The patient is a female aged 18–29, an image taken at a distance, the affected area is the arm and leg — 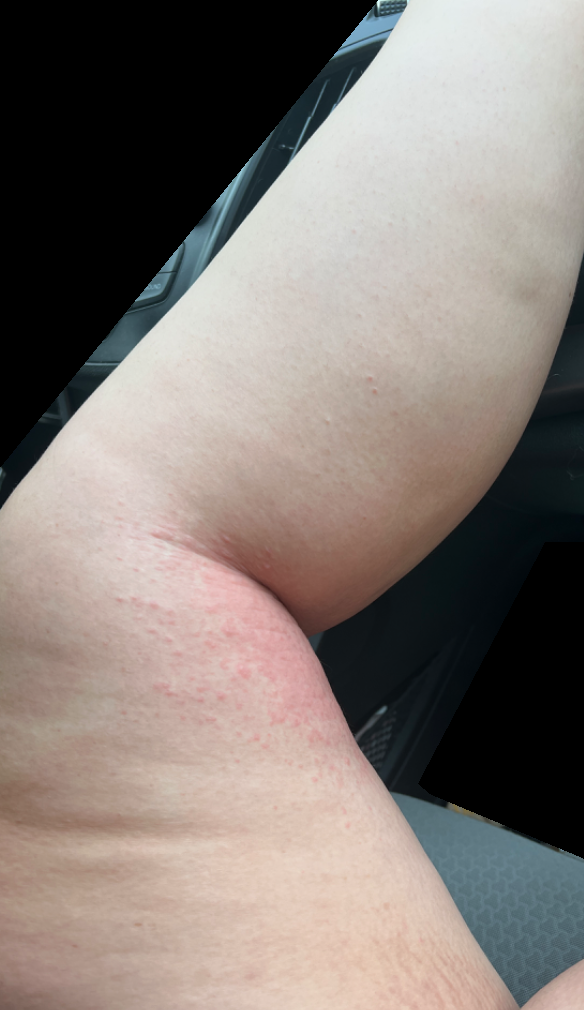Impression: The case was difficult to assess from the available photograph.